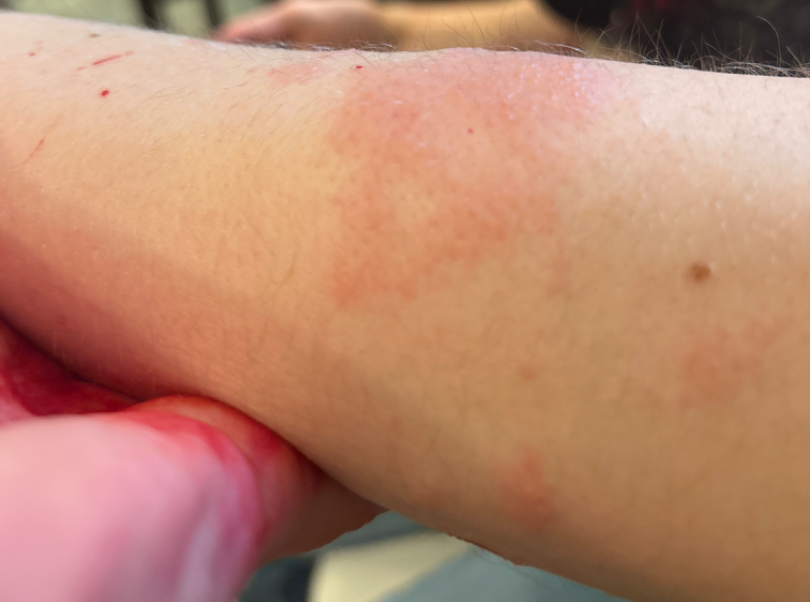Acute dermatitis, NOS (most likely).